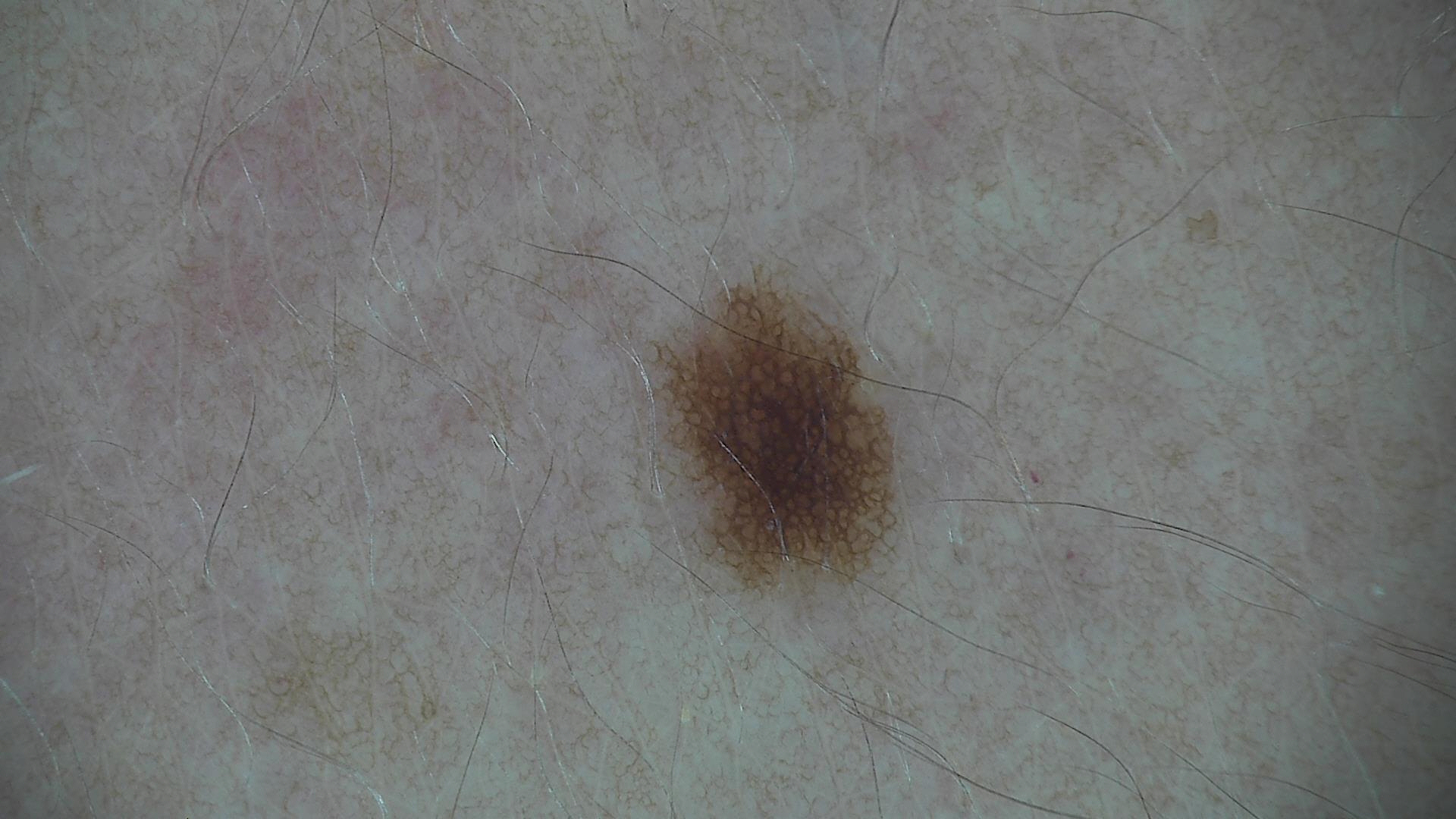Q: What was the diagnostic impression?
A: dysplastic junctional nevus (expert consensus)